A dermoscopic close-up of a skin lesion; a male subject, aged 68 to 72:
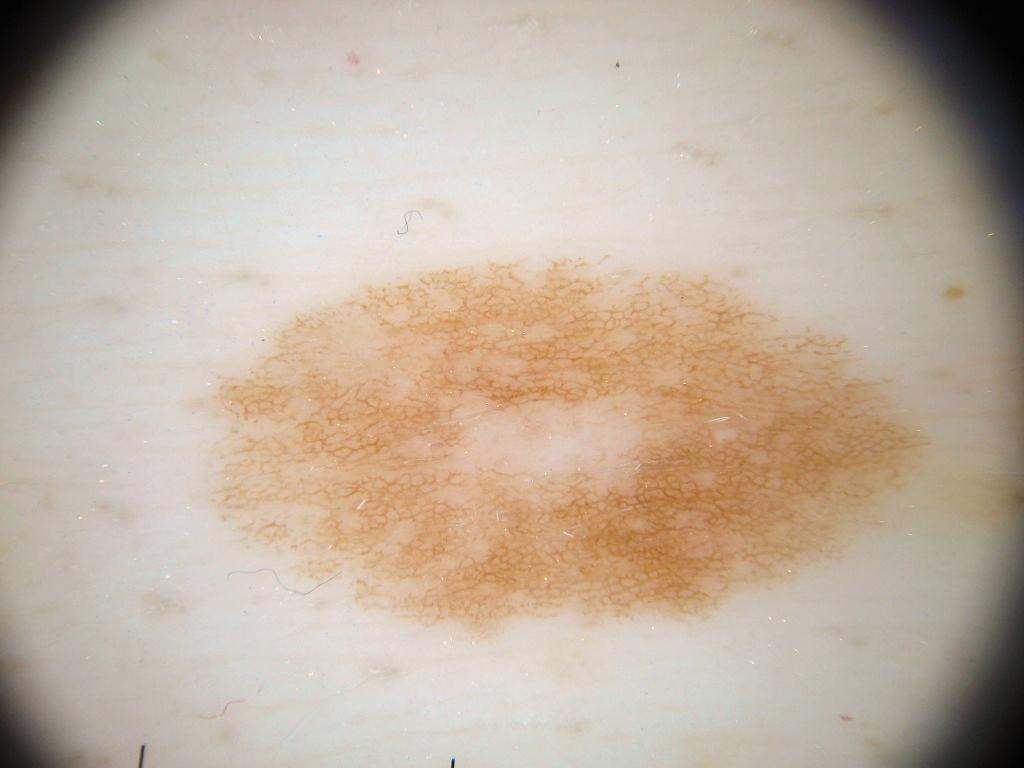Dermoscopic assessment notes pigment network, with no streaks, globules, milia-like cysts, or negative network.
The lesion covers approximately 32% of the dermoscopic field.
With coordinates (x1, y1, x2, y2), the lesion is located at <box>173, 238, 941, 661</box>.
Expert review diagnosed this as a melanocytic nevus, a benign lesion.